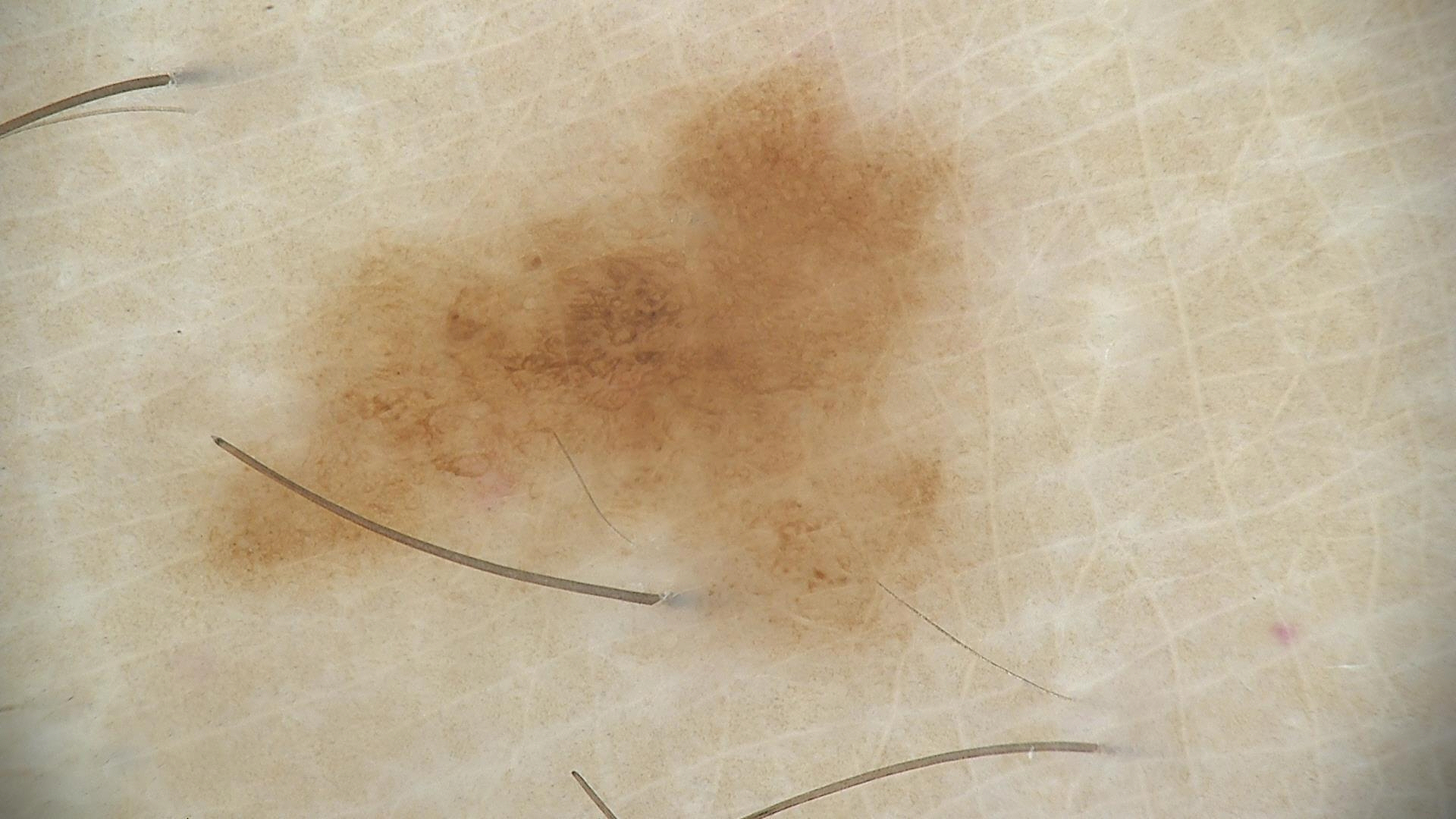- assessment — dysplastic junctional nevus (expert consensus)